The patient was assessed as Fitzpatrick II.
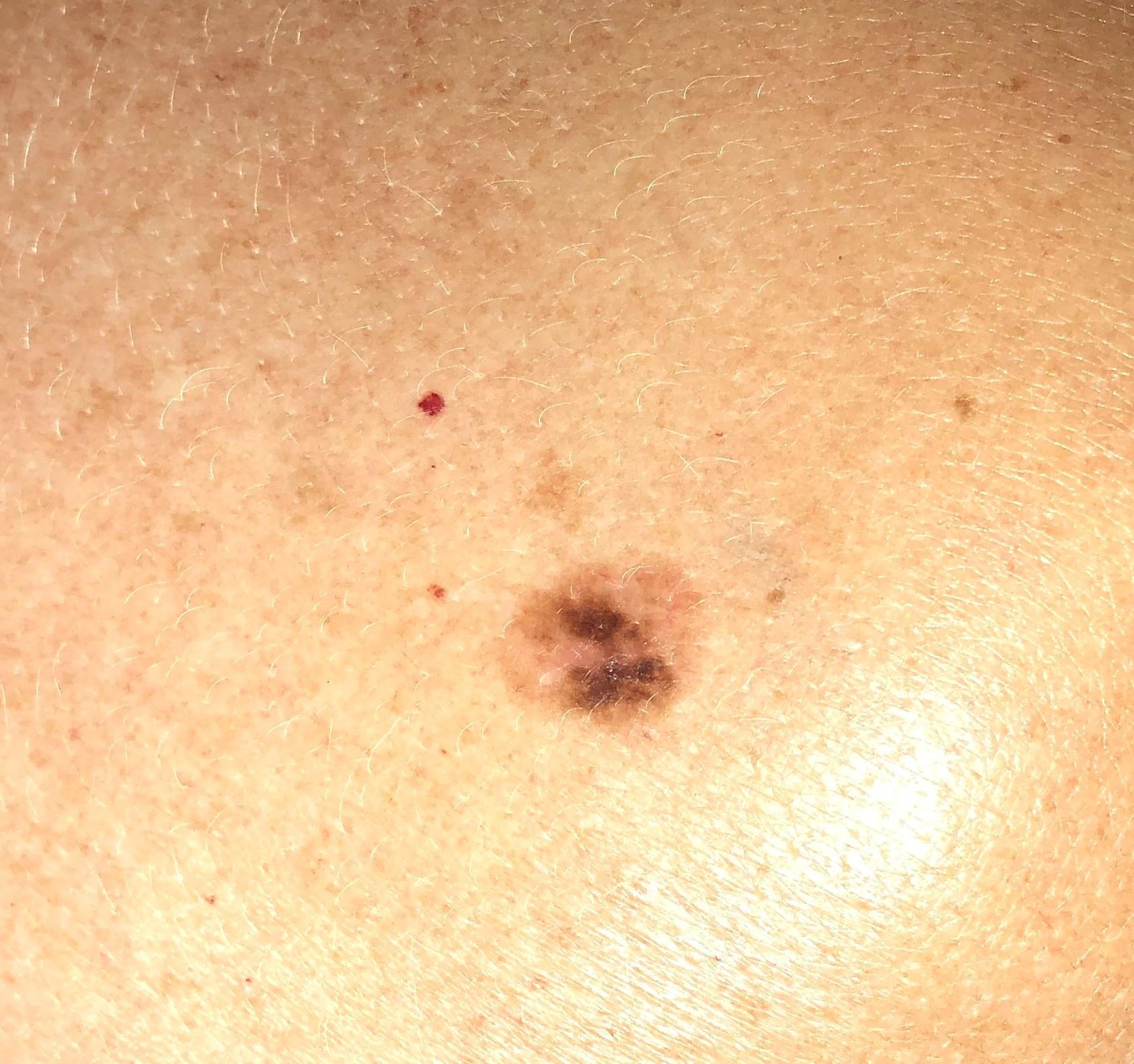  diagnosis:
    name: Nevus
    malignancy: benign
    confirmation: histopathology
    lineage: melanocytic